The patient is FST II; a male subject aged approximately 70.
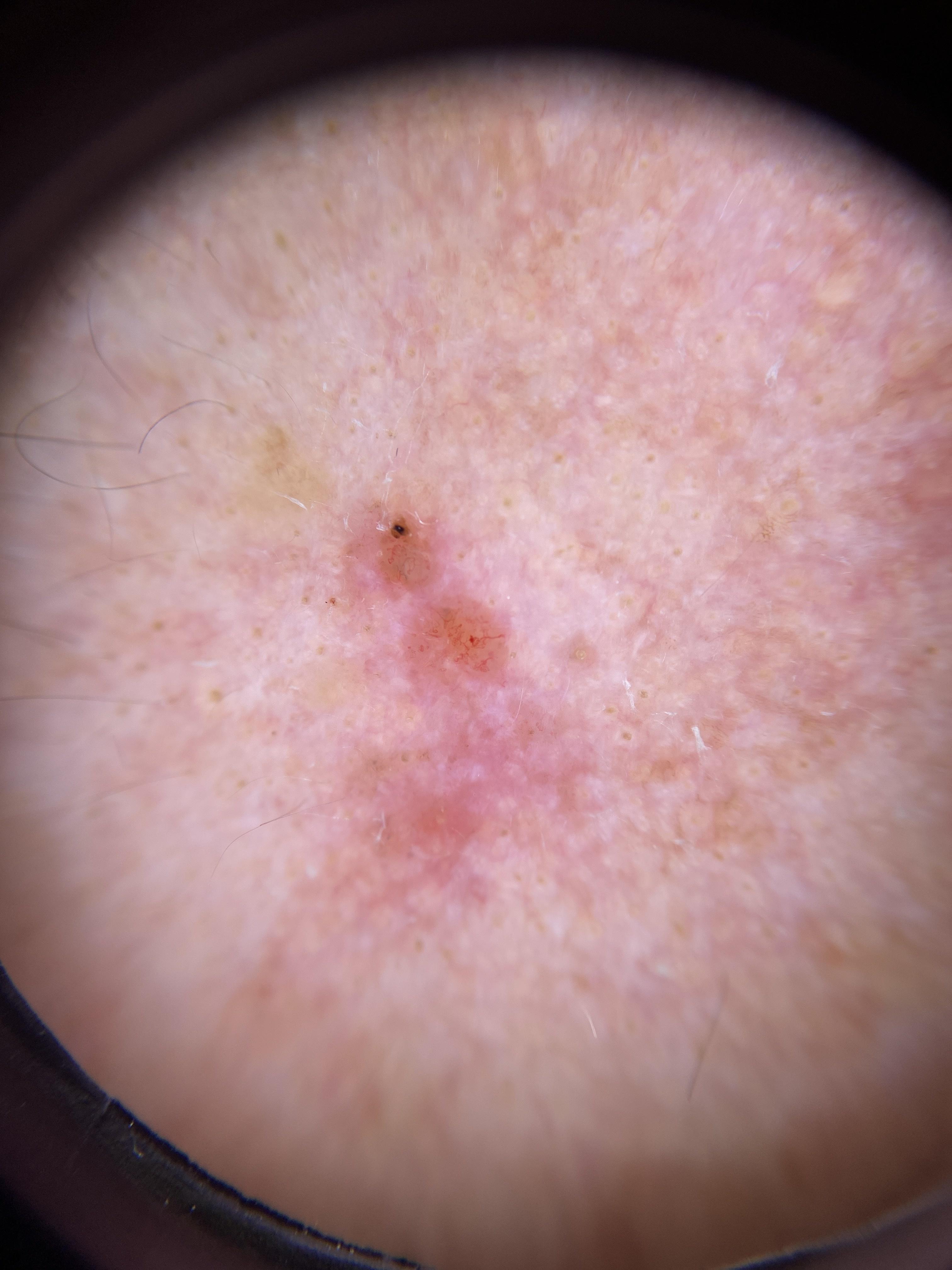Q: Where is the lesion located?
A: the head or neck
Q: What is this lesion?
A: Basal cell carcinoma (biopsy-proven)